A dermoscopy image of a single skin lesion.
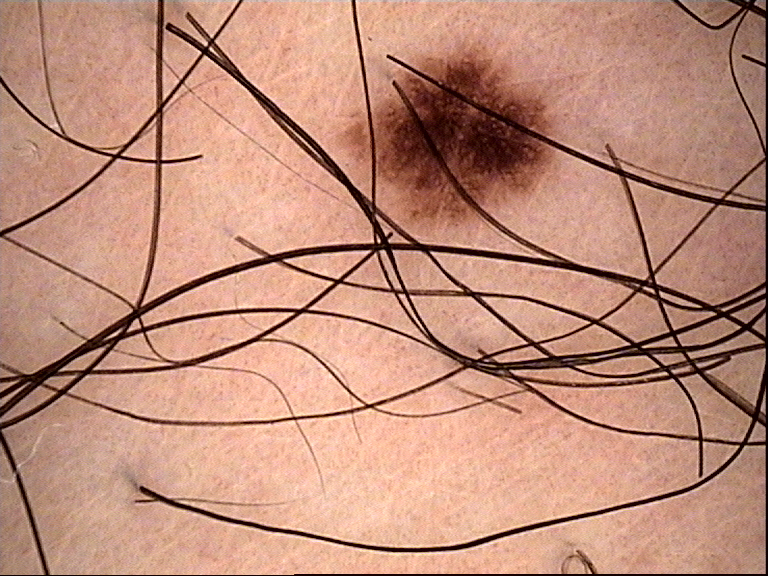label: dysplastic junctional nevus (expert consensus)